A skin lesion imaged with a dermatoscope. The subject is a female aged 53-57.
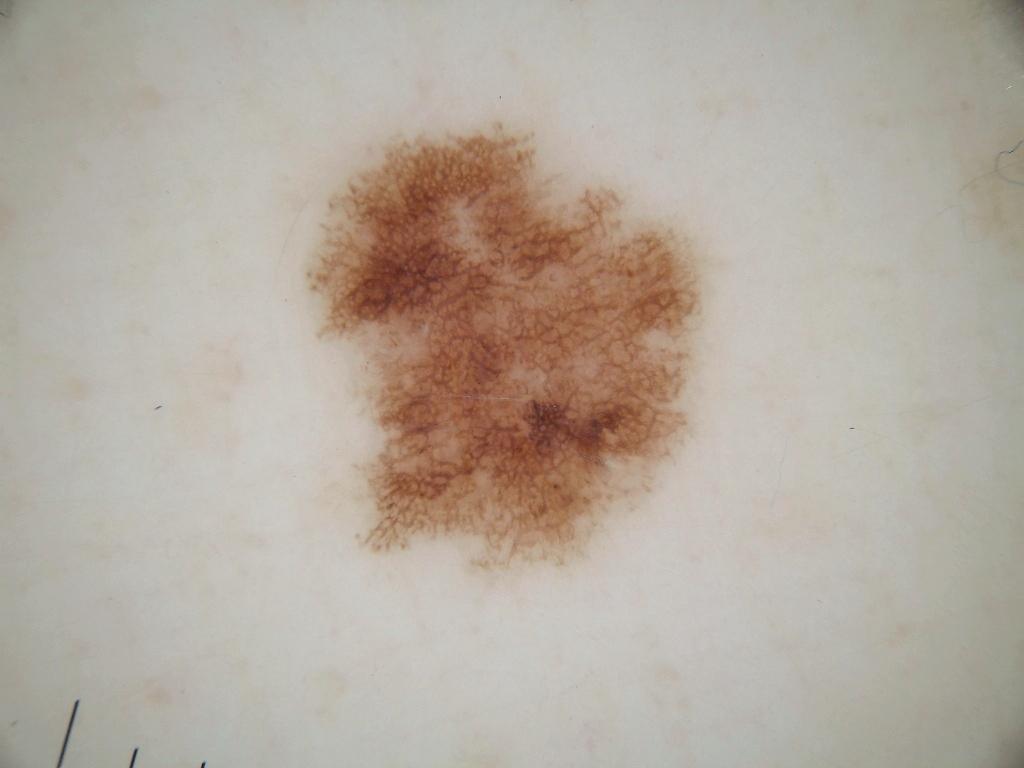Case summary:
Dermoscopically, the lesion shows pigment network and globules. As (left, top, right, bottom), the lesion spans [291,112,716,580].
Assessment:
Diagnosed as a melanocytic nevus.